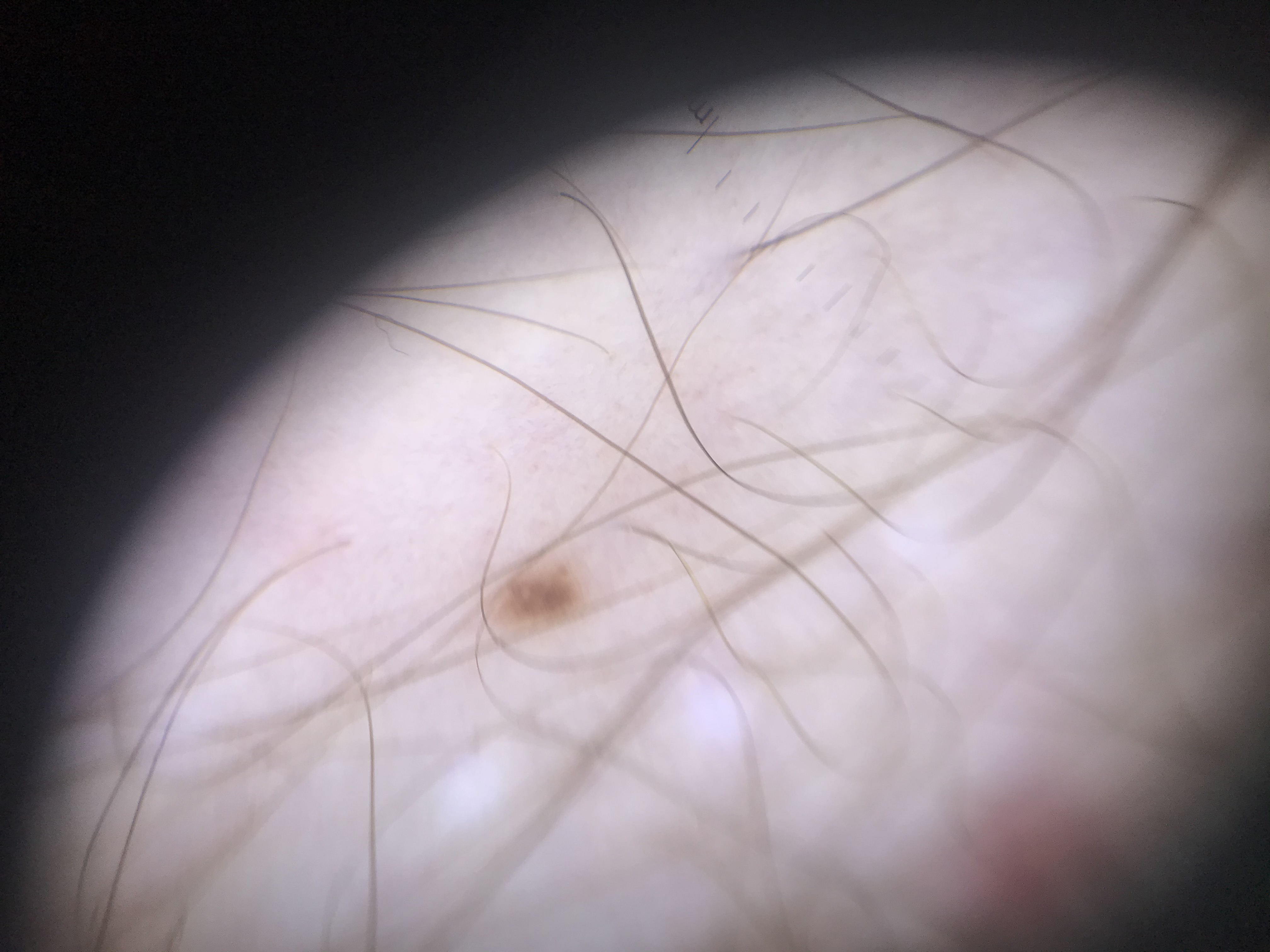<case>
<image>dermoscopy</image>
<lesion_type>
<main_class>banal</main_class>
<pattern>junctional</pattern>
</lesion_type>
<diagnosis>
<name>junctional nevus</name>
<code>jb</code>
<malignancy>benign</malignancy>
<super_class>melanocytic</super_class>
<confirmation>expert consensus</confirmation>
</diagnosis>
</case>